A close-up photograph · the lesion involves the back of the torso · female subject, age 40–49: 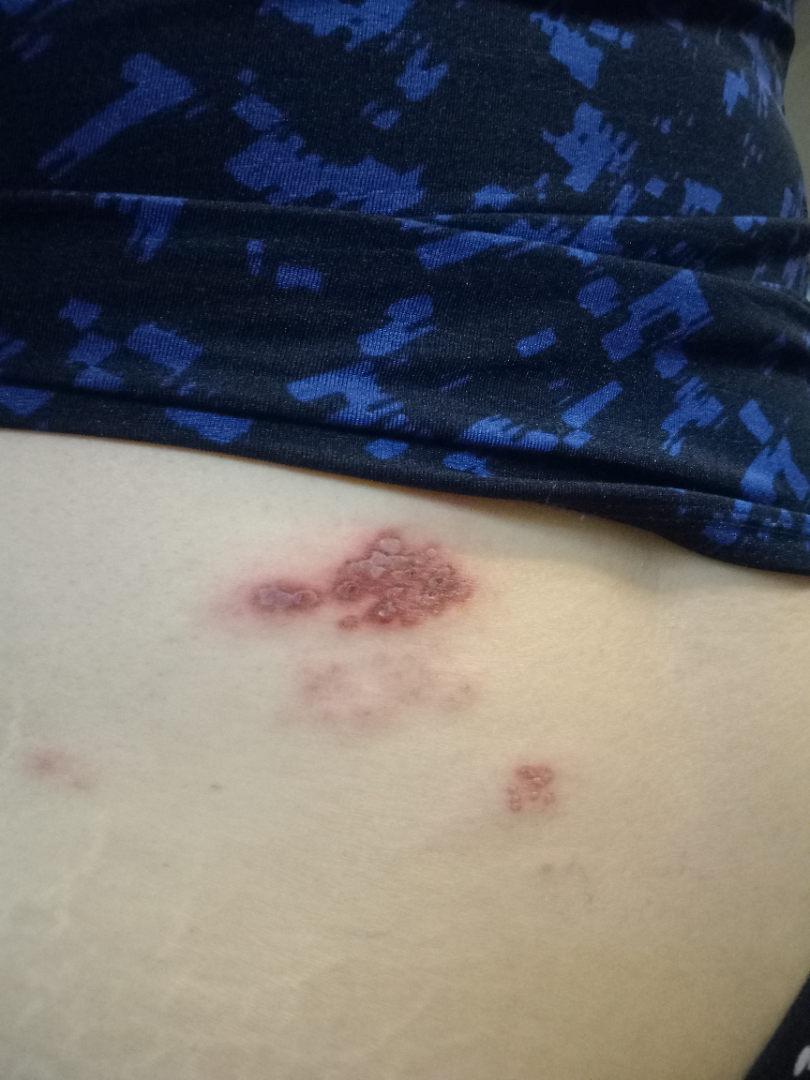| feature | finding |
|---|---|
| differential diagnosis | one reviewing dermatologist: Herpes Zoster and Herpes Simplex were considered with similar weight |